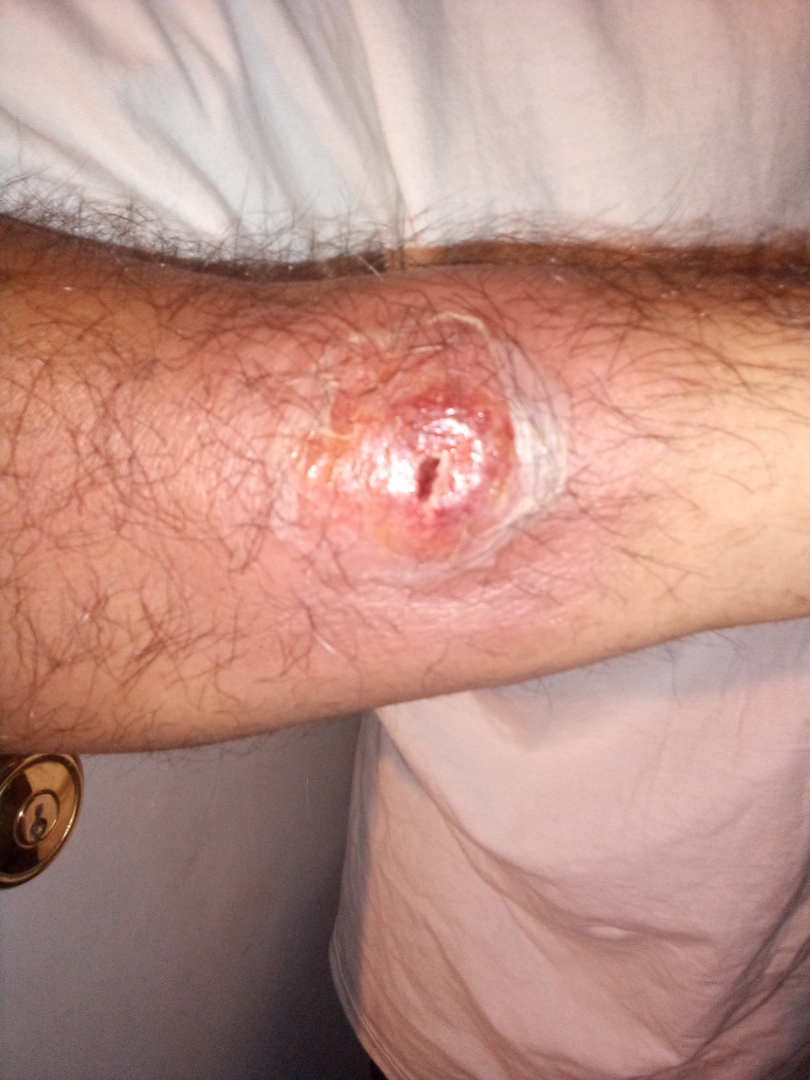assessment: indeterminate | image framing: at a distance | other reported symptoms: none reported | present for: one to three months | contributor: male | texture: raised or bumpy and fluid-filled | body site: leg and arm | patient-reported symptoms: bleeding, pain and bothersome appearance.